This image was taken at an angle · the front of the torso and head or neck are involved · the patient is a female aged 40–49: 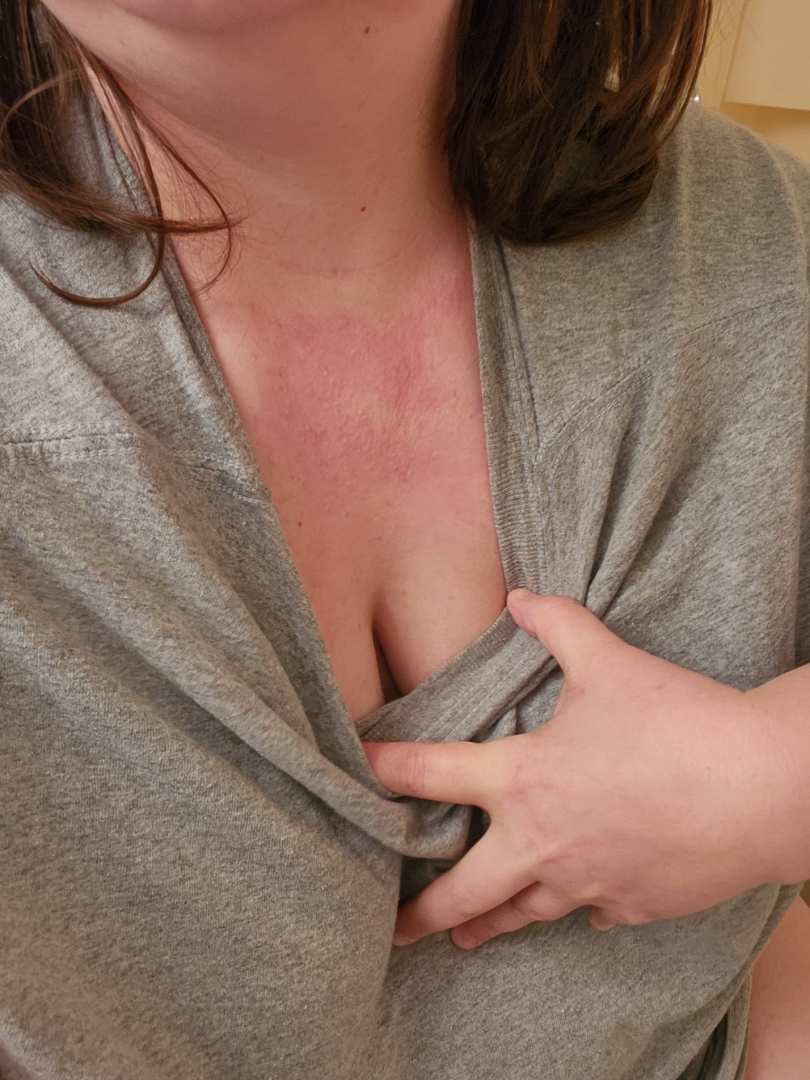symptoms=itching, enlargement and burning | other reported symptoms=fatigue and shortness of breath | skin tone=FST II | symptom duration=less than one week | lesion texture=rough or flaky and raised or bumpy | clinical impression=most likely Allergic Contact Dermatitis; the differential also includes Photodermatitis; a more distant consideration is Drug Rash; less likely is Acute dermatitis, NOS; less probable is Rosacea.